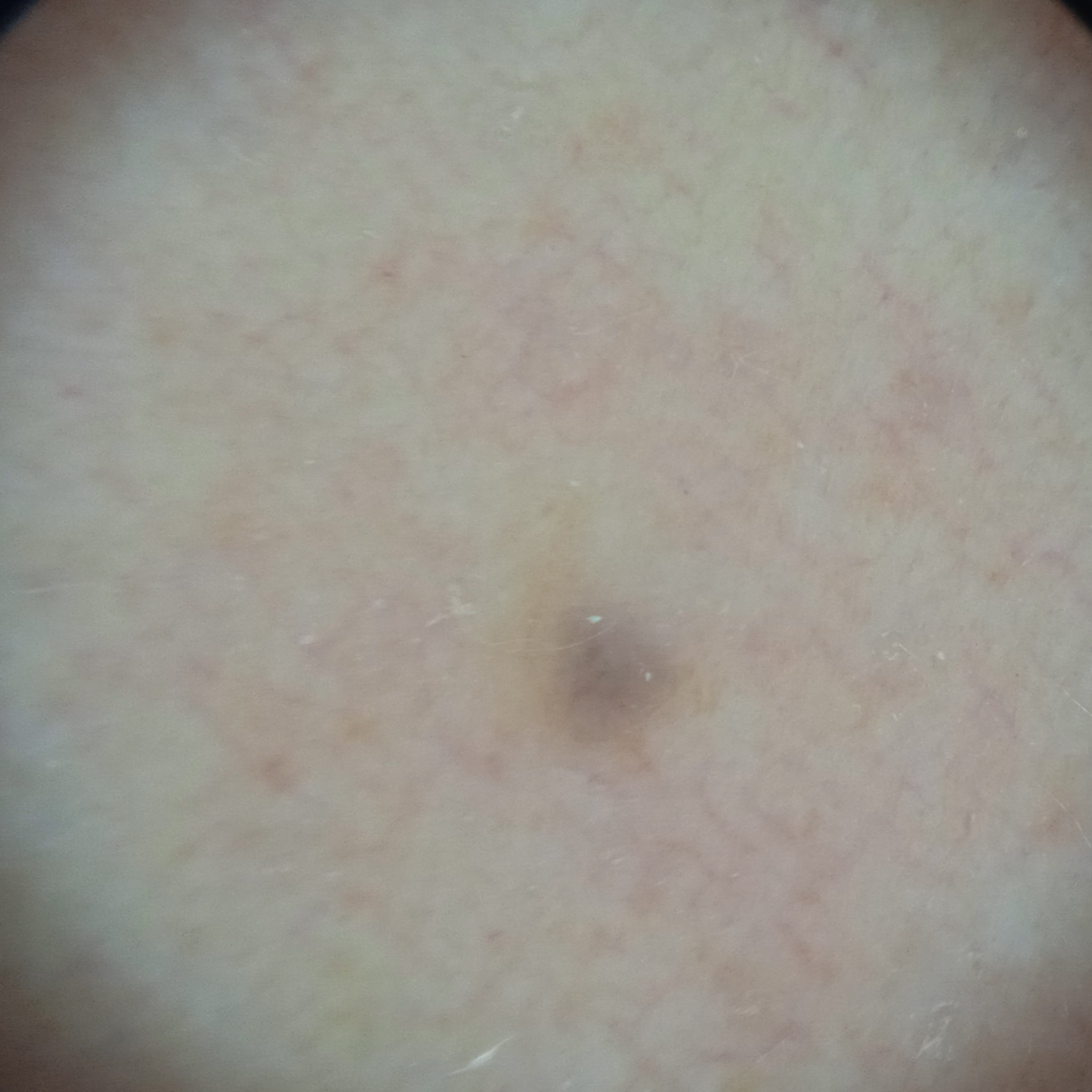A dermatoscopic image of a skin lesion.
Collected as part of a research study, without a referral diagnosis.
Few moles overall by the patient's own estimate.
A female subject 48 years of age.
By self-report, a history of sunbed use and a family history of skin cancer.
Measuring roughly 1.8 mm.
The lesion was assessed as a melanocytic nevus.